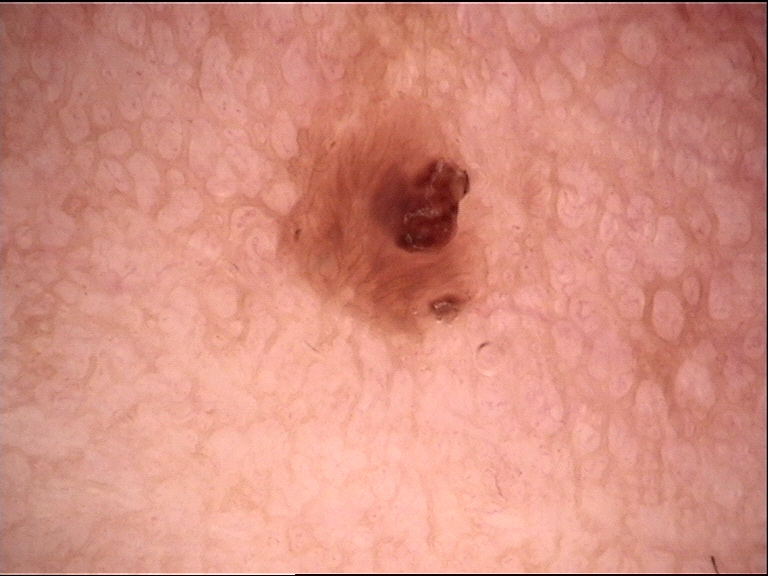The diagnosis was a compound nevus.